A dermoscopic image of a skin lesion.
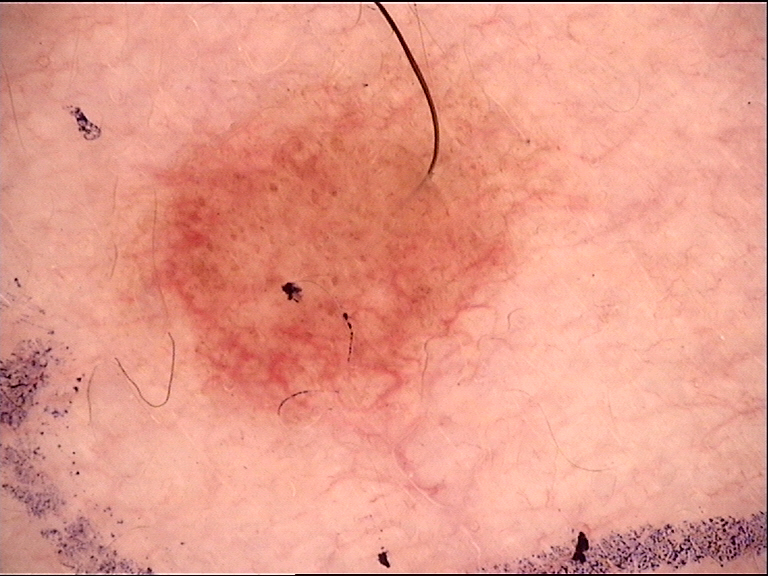The diagnostic label was a benign lesion — a dysplastic junctional nevus.